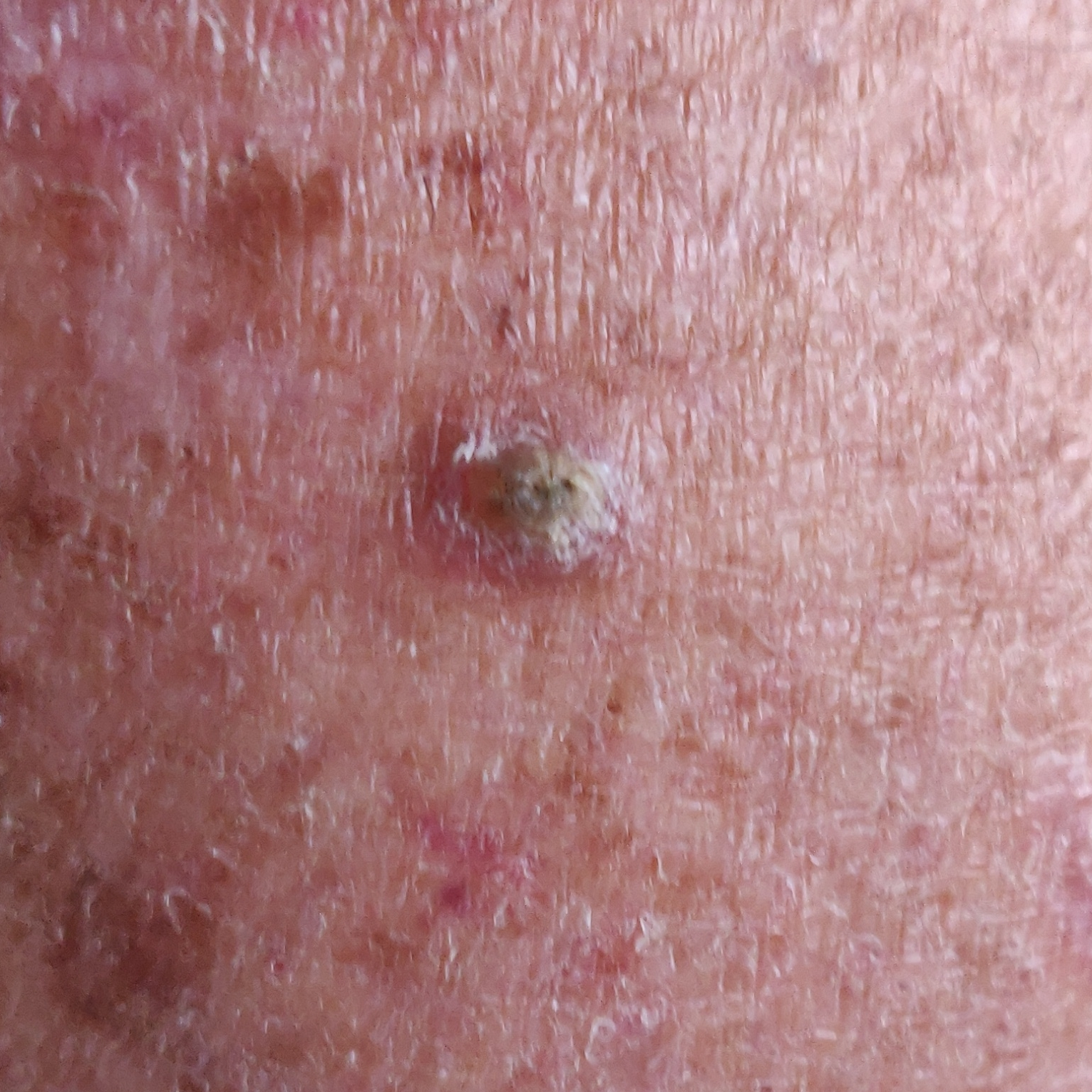Q: How was this image acquired?
A: clinical photo
Q: Where on the body is the lesion?
A: a thigh
Q: What does the patient describe?
A: elevation, itching, growth
Q: What is this lesion?
A: actinic keratosis (biopsy-proven)